Contact-polarized dermoscopy of a skin lesion; a male subject approximately 40 years of age — 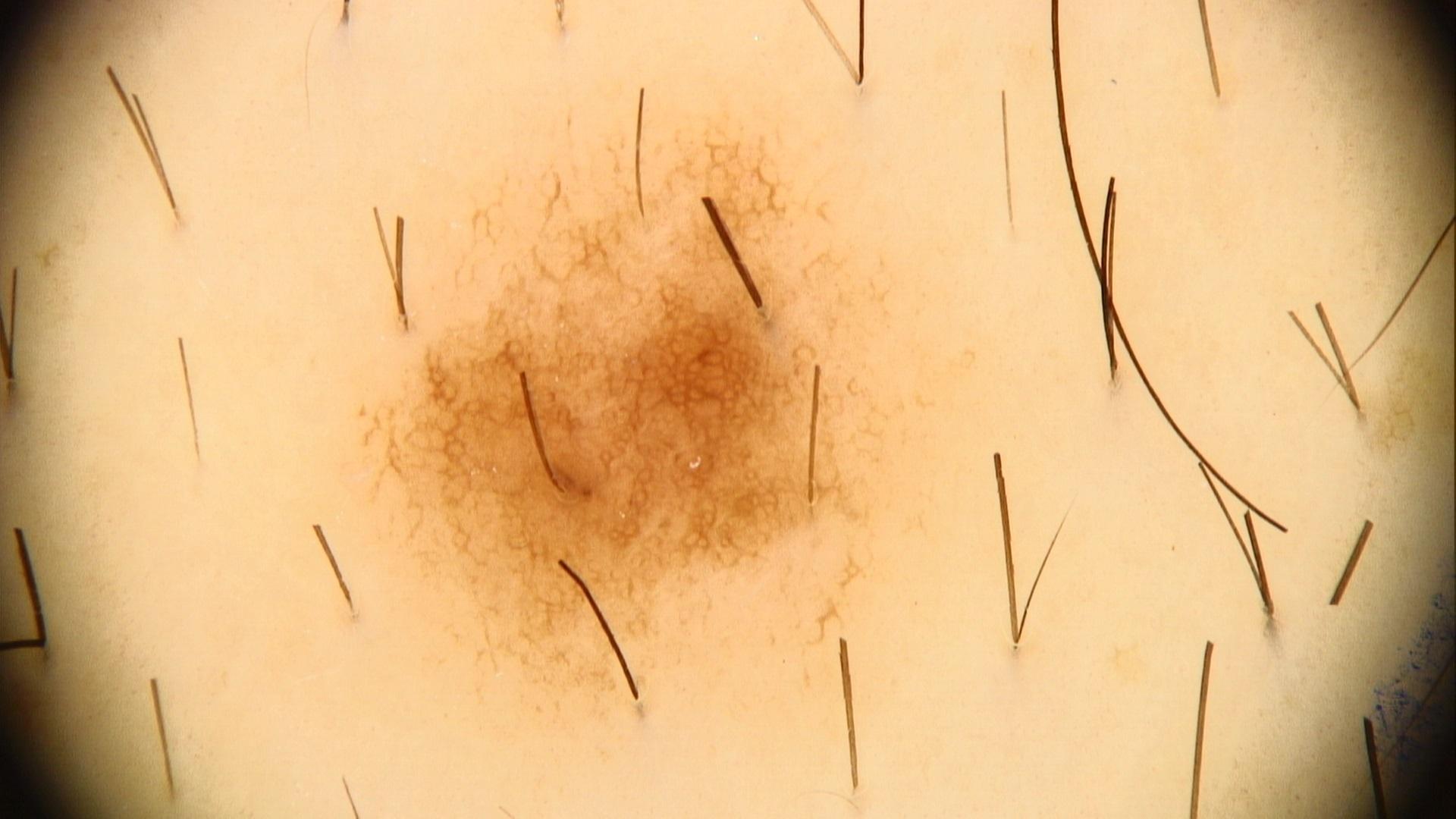The lesion is on the trunk. Expert review favored a benign lesion — a nevus.